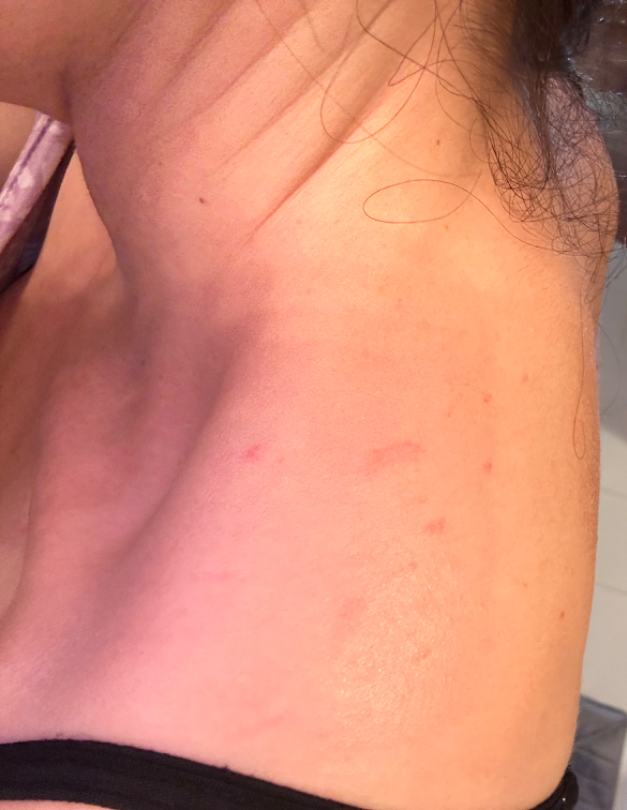This is a close-up image.
Fitzpatrick skin type III; human graders estimated Monk skin tone scale 3.
Allergic Contact Dermatitis (weight 0.54); Acne (weight 0.23); Folliculitis (weight 0.23).